The subject is 18–29, female; this is a close-up image; the affected area is the arm — 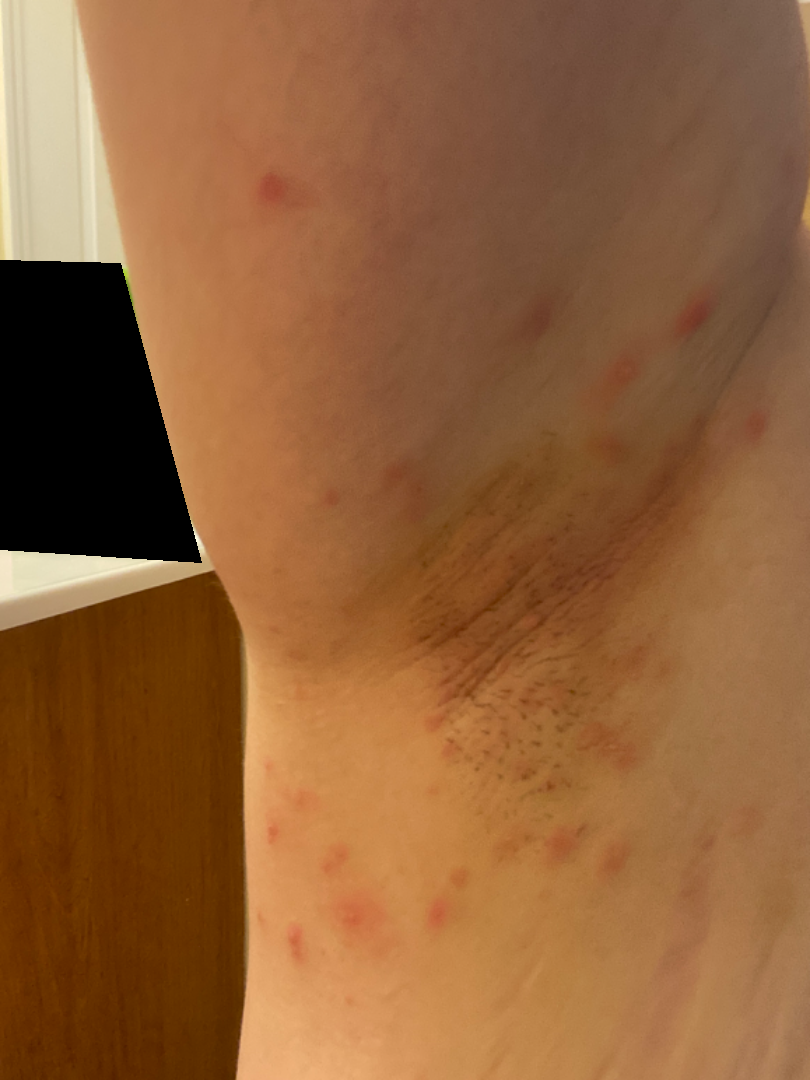Skin tone: Fitzpatrick II; lay graders estimated 3 on the Monk Skin Tone. The condition has been present for less than one week. Reported lesion symptoms include itching. No relevant systemic symptoms. The contributor notes the lesion is raised or bumpy and fluid-filled. On photographic review by a dermatologist, the favored diagnosis is Insect Bite; possibly Folliculitis; with consideration of Irritant Contact Dermatitis.